Texture is reported as raised or bumpy · Fitzpatrick skin type III · the patient reports bothersome appearance, itching and burning · this image was taken at an angle · the affected area is the leg and arm · the patient described the issue as a rash · reported duration is about one day — 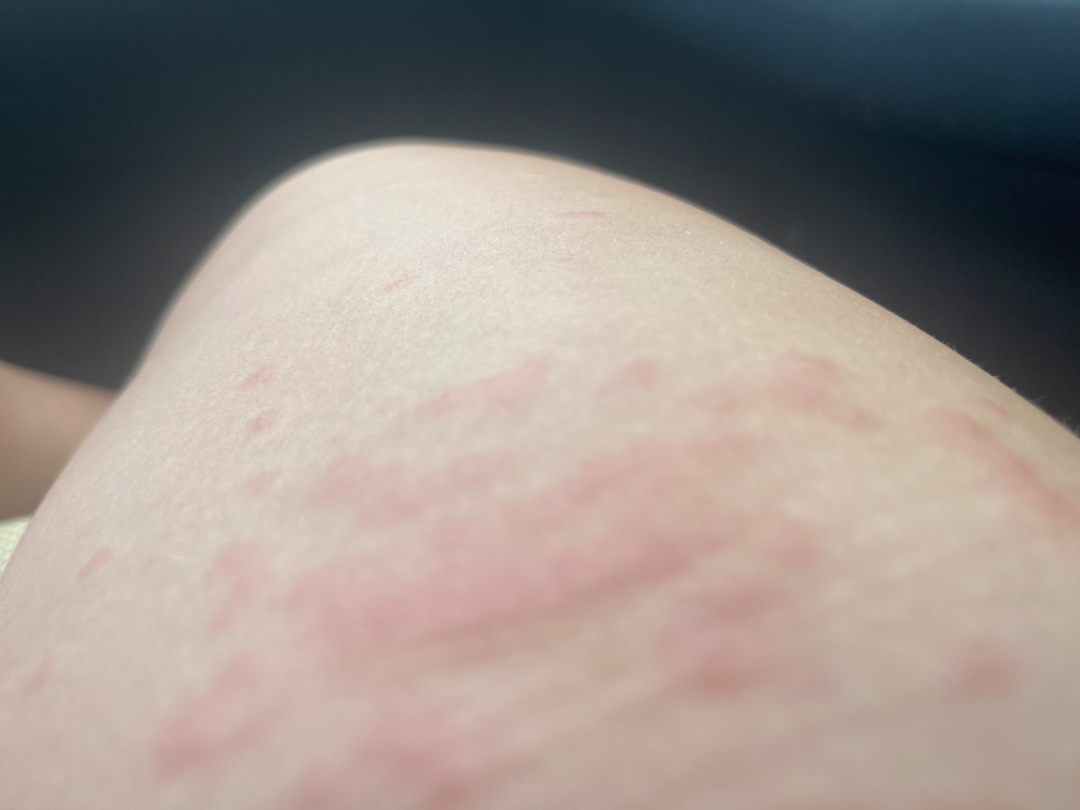Findings:
- assessment · ungradable on photographic review